Dermoscopy of a skin lesion. Collected as part of a research study, without a referral diagnosis. A female patient 67 years old.
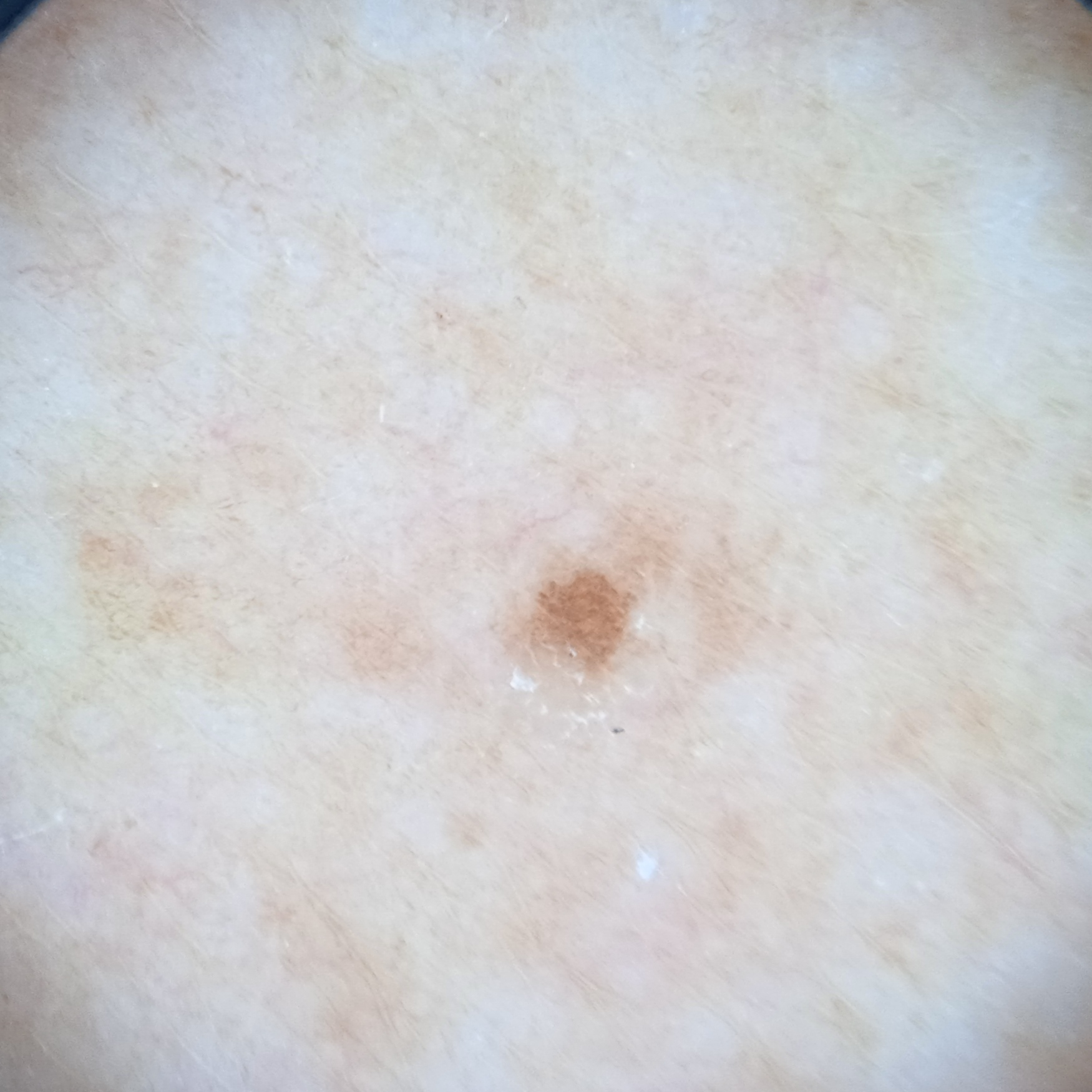The lesion is located on an arm. The lesion measures approximately 1.3 mm. The dermatologists' assessment was a melanocytic nevus.